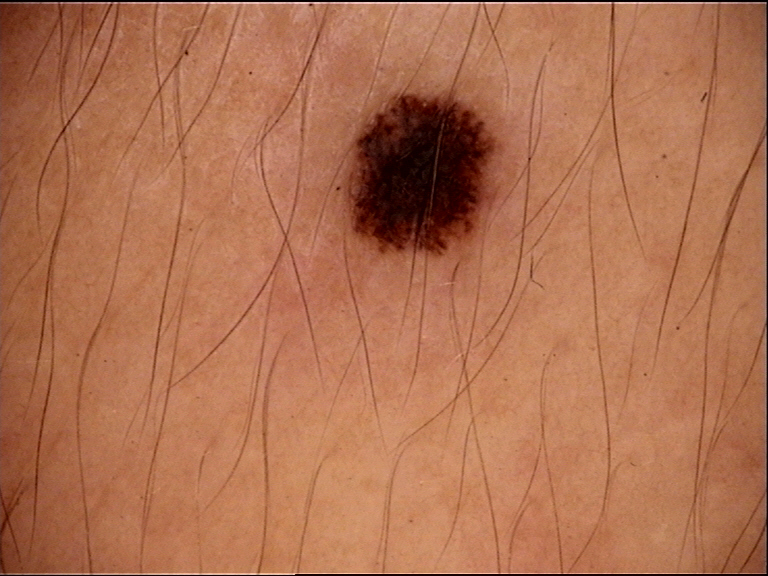Dermoscopy of a skin lesion. The diagnosis was a junctional nevus.